This image was taken at a distance; the patient is a female aged 18–29; the affected area is the leg.
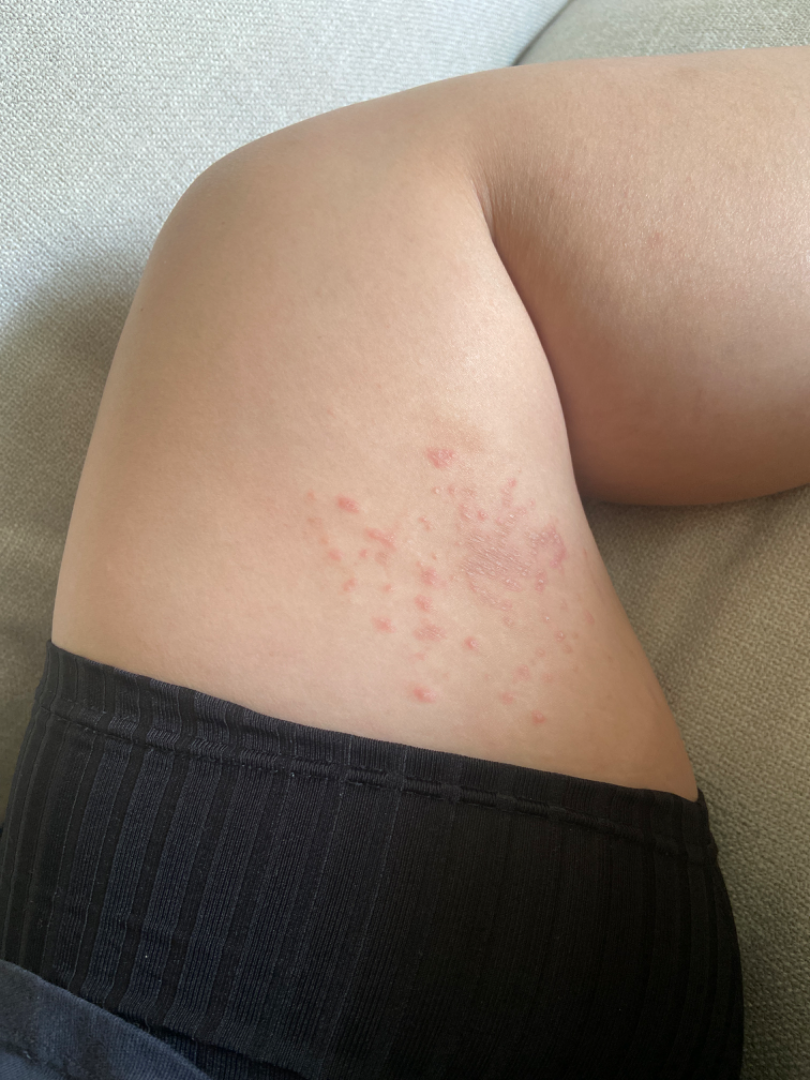Texture is reported as rough or flaky and raised or bumpy. Skin tone: Fitzpatrick II; lay graders estimated Monk skin tone scale 2. The patient considered this a rash. Psoriasis (considered); Lichen planus/lichenoid eruption (considered); Eczema (considered); Insect Bite (remote); Allergic Contact Dermatitis (remote).